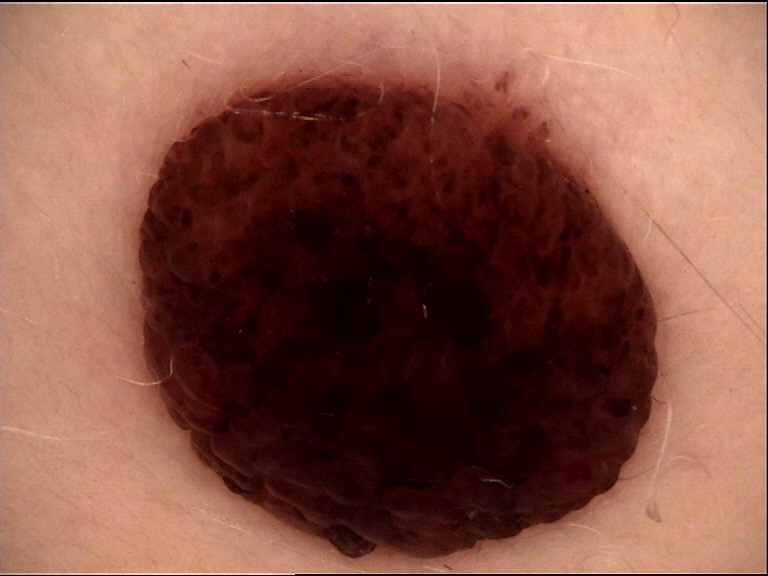imaging: dermoscopy | subtype: banal | label: dermal nevus (expert consensus).